The photograph was taken at an angle. The lesion involves the head or neck:
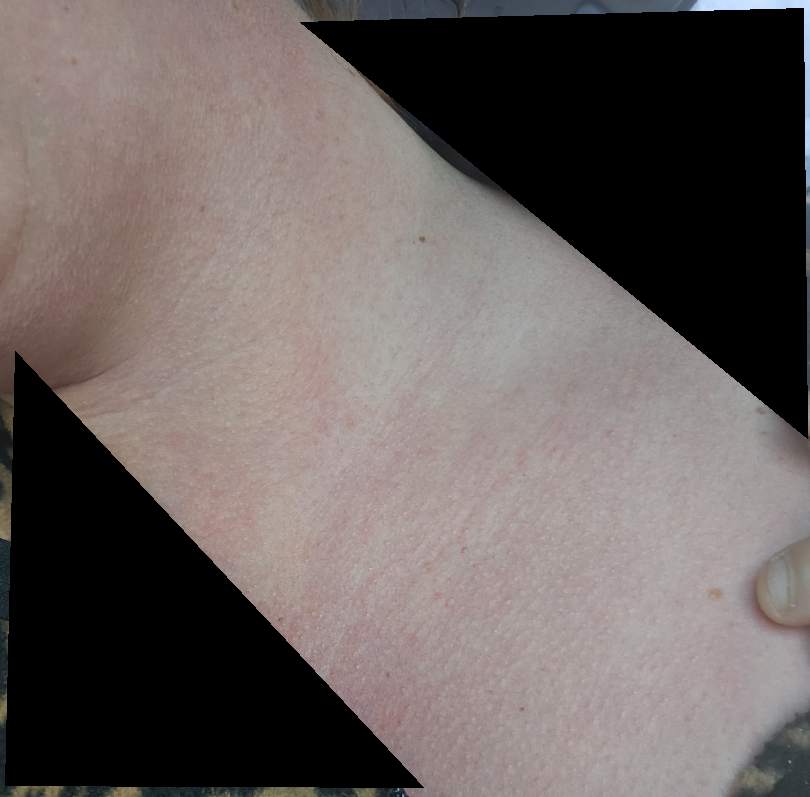Diagnostic features were not clearly distinguishable in this photograph.
The patient notes the lesion is raised or bumpy.
Reported lesion symptoms include bothersome appearance and itching.